The patient reports associated joint pain and fatigue · reported duration is less than one week · the subject is a male aged 30–39 · symptoms reported: pain, bothersome appearance, burning and enlargement · close-up view · located on the leg.
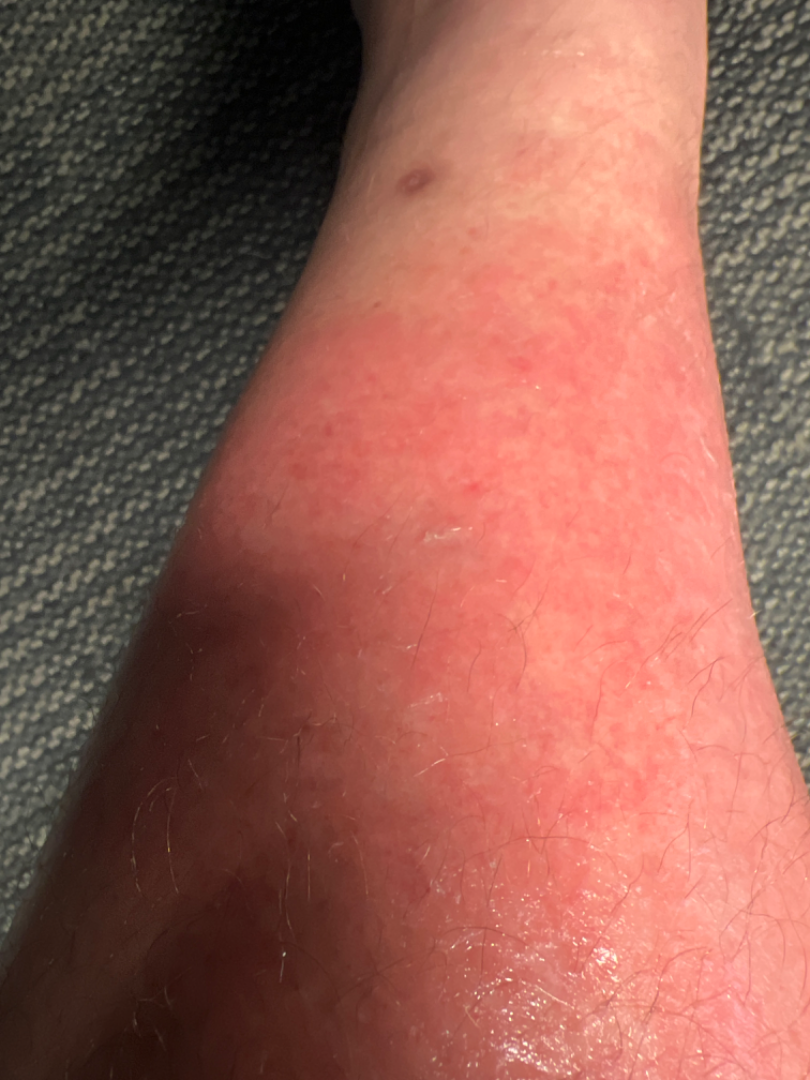The dermatologist could not determine a likely condition from the photograph alone.